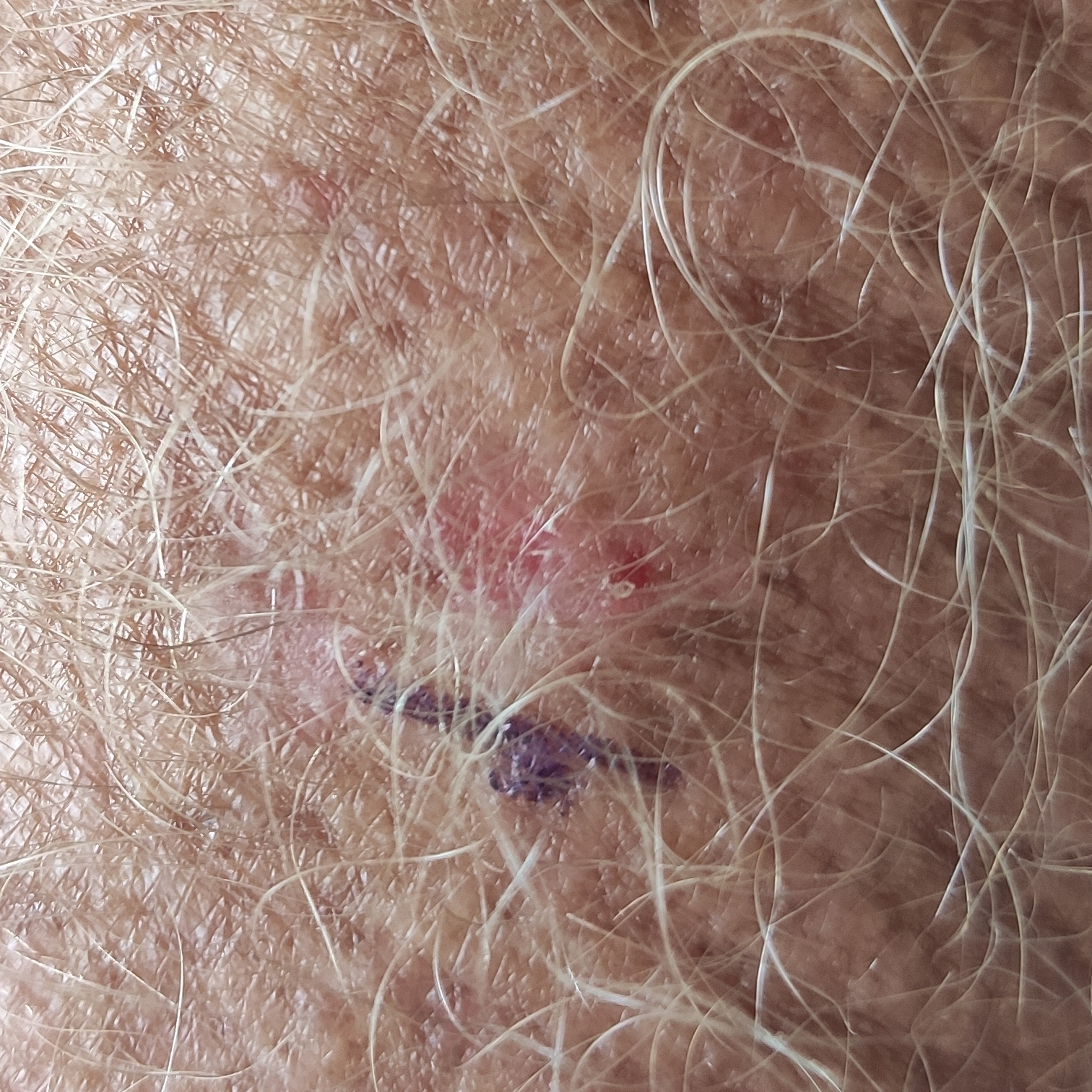Impression: Clinically diagnosed as an actinic keratosis.